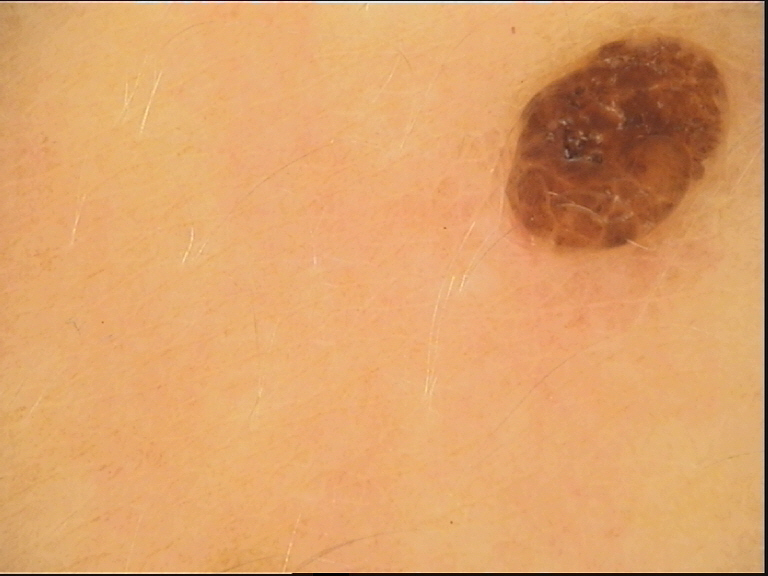This is a banal lesion. Classified as a compound nevus.